Male patient, age 18–29. The leg is involved. The photograph is a close-up of the affected area.
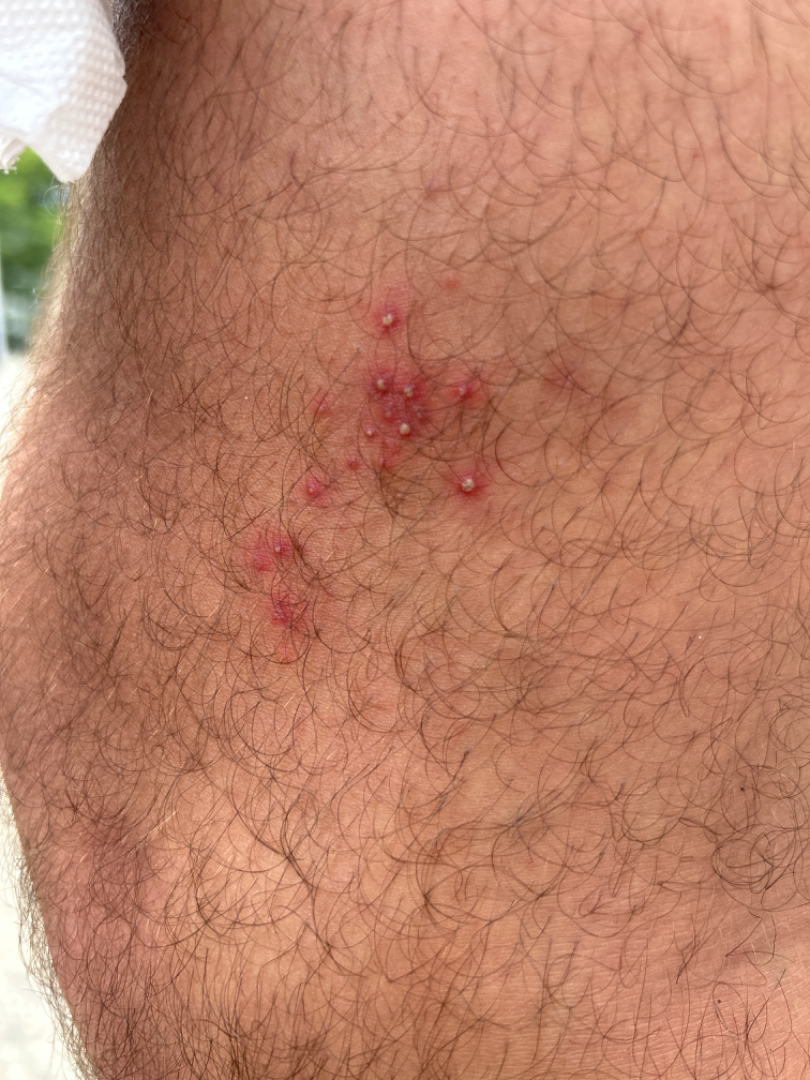The patient did not report lesion symptoms. Self-categorized by the patient as a rash. The lesion is described as raised or bumpy and fluid-filled. In keeping with Folliculitis.